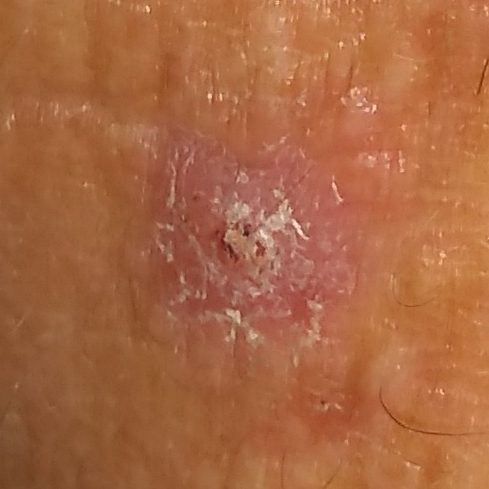{"image": "clinical photograph", "patient": {"age": 55, "gender": "male"}, "risk_factors": {"positive": ["pesticide exposure", "smoking", "alcohol use"]}, "lesion_location": "an arm", "lesion_size": {"diameter_1_mm": 7.0, "diameter_2_mm": 7.0}, "diagnosis": {"name": "squamous cell carcinoma", "code": "SCC", "malignancy": "malignant", "confirmation": "histopathology"}}